The subject is 30–39, male. The photograph is a close-up of the affected area. The lesion involves the arm: 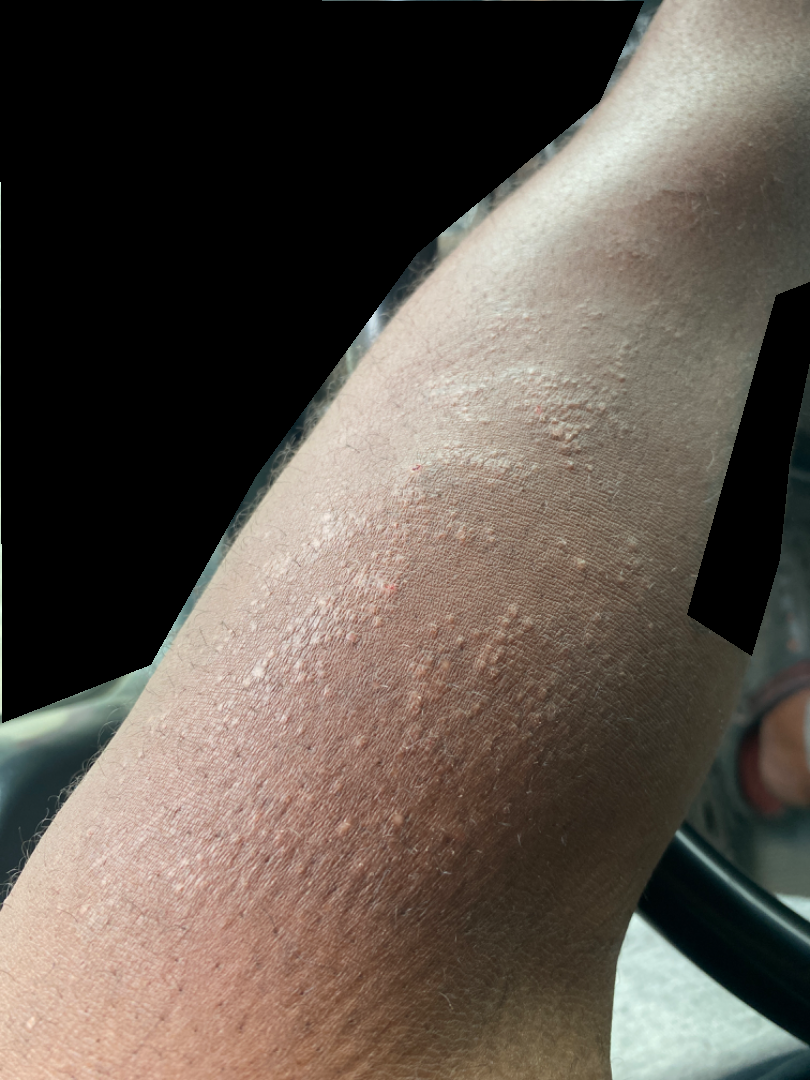{
  "differential": {
    "tied_lead": [
      "Chronic dermatitis, NOS",
      "Amyloidosis of skin"
    ],
    "unlikely": [
      "Lichen Simplex Chronicus",
      "Lichen planus/lichenoid eruption",
      "Eczema"
    ]
  }
}